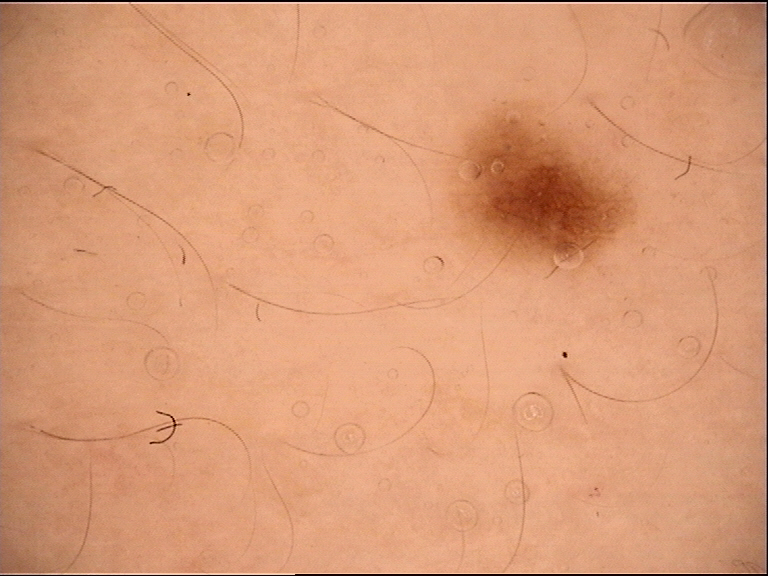imaging=dermoscopy
label=dysplastic junctional nevus (expert consensus)